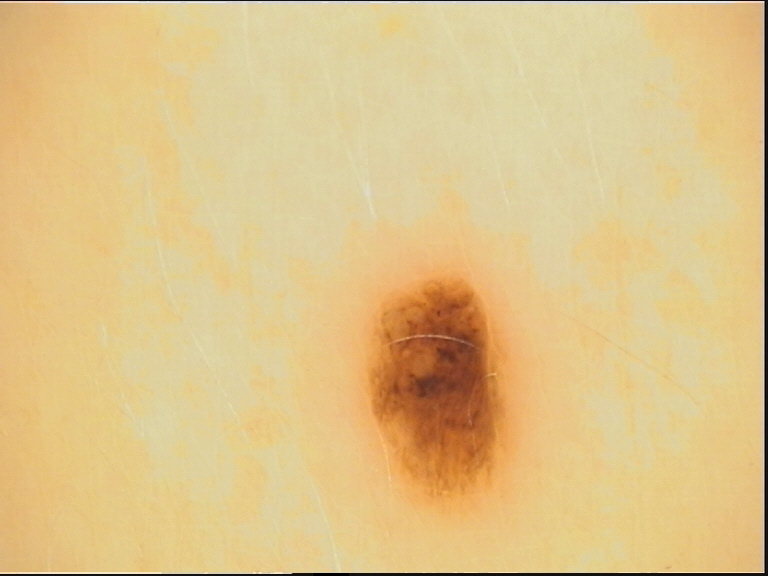modality = dermatoscopy, class = compound nevus (expert consensus).